Dermoscopy of a skin lesion.
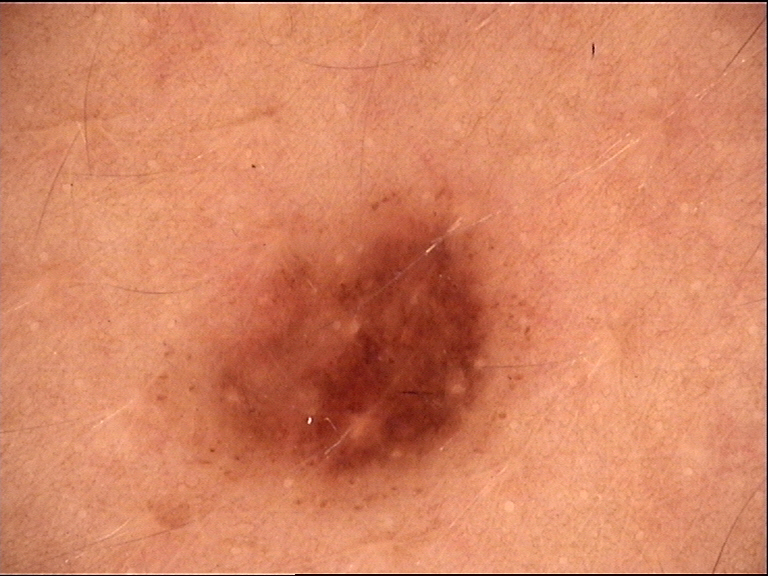Impression: Consistent with a benign lesion — a dysplastic junctional nevus.